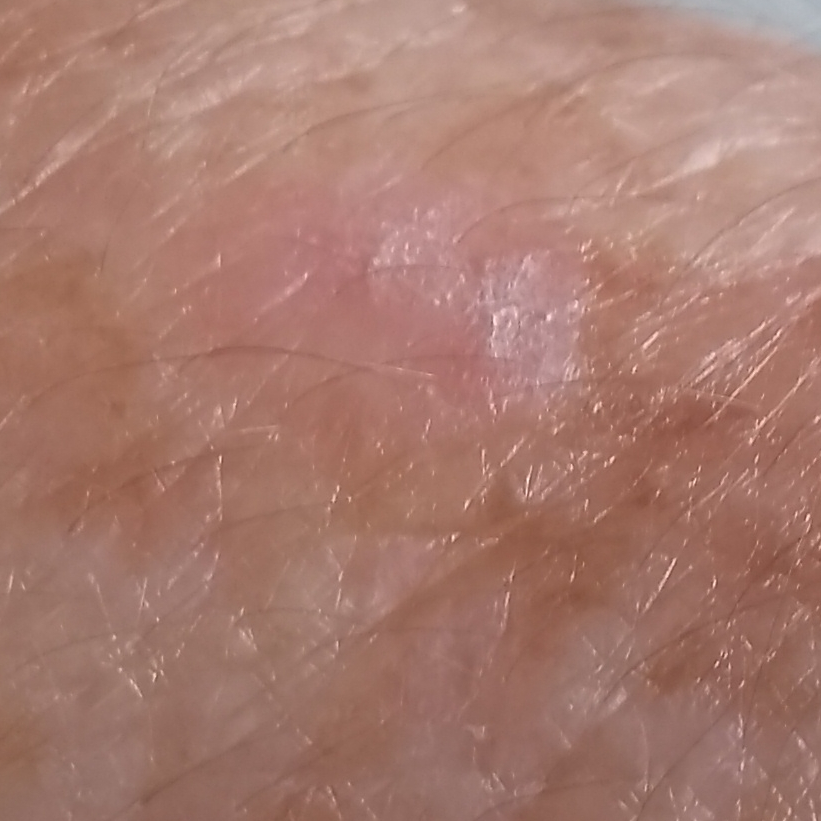<lesion>
<diagnosis>
<name>actinic keratosis</name>
<code>ACK</code>
<malignancy>indeterminate</malignancy>
<confirmation>clinical consensus</confirmation>
</diagnosis>
</lesion>